A clinical close-up photograph of a skin lesion; a female subject in their mid-50s: 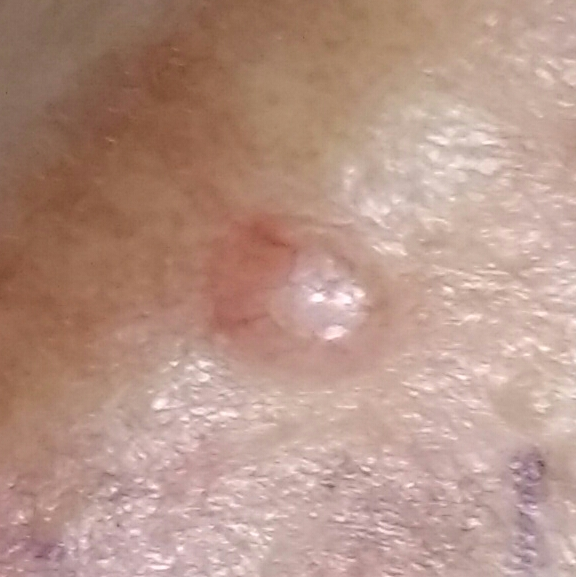The lesion involves the nose. By the patient's account, the lesion has grown, itches, and is elevated. Histopathology confirmed a basal cell carcinoma.